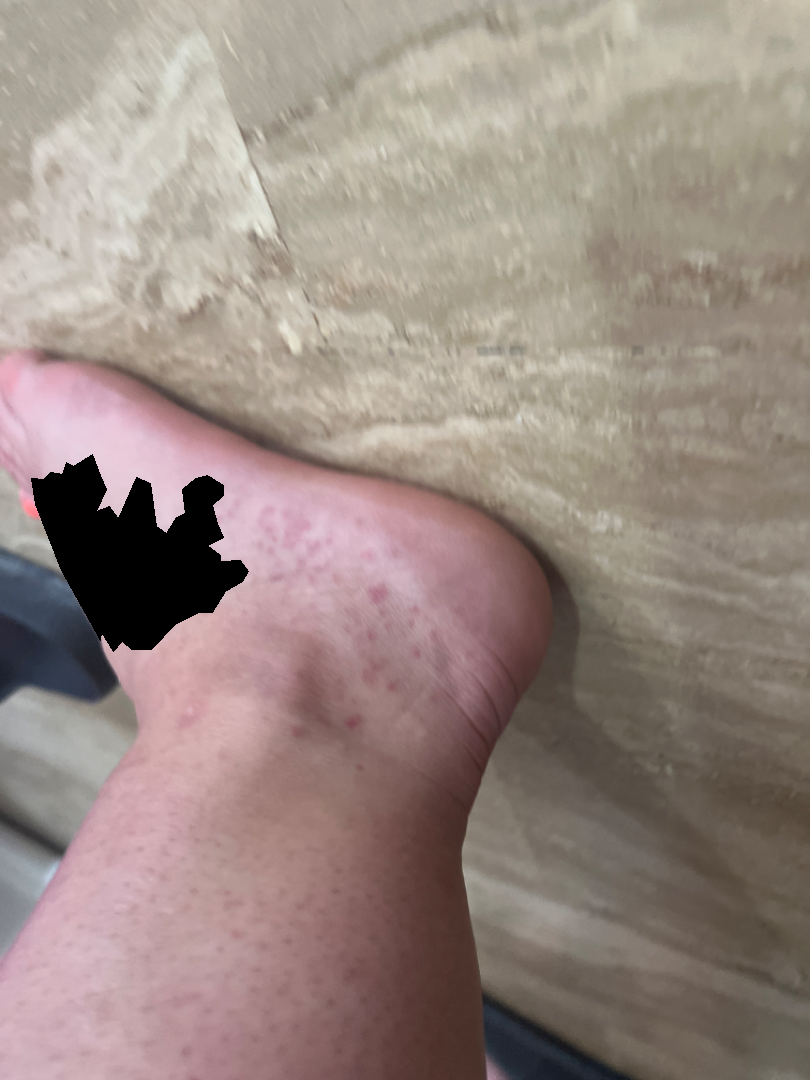Symptoms reported: bothersome appearance. The photograph was taken at an angle. Texture is reported as raised or bumpy. Female patient, age 30–39. Self-categorized by the patient as a rash. The patient reports associated joint pain. Reported duration is less than one week. The affected area is the sole of the foot, back of the hand, top or side of the foot and leg. The leading consideration is Lichen planus/lichenoid eruption; an alternative is Psoriasis; also raised was Eczema.